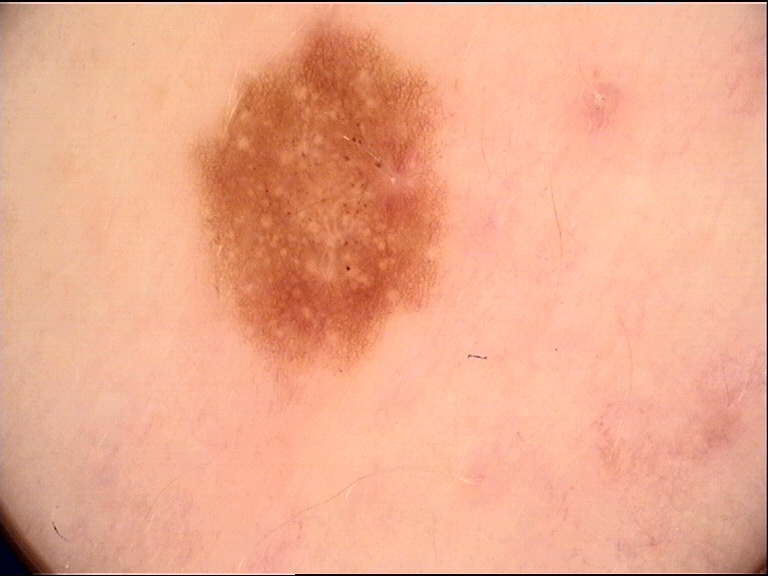A dermoscopic image of a skin lesion.
Diagnosed as a dysplastic junctional nevus.